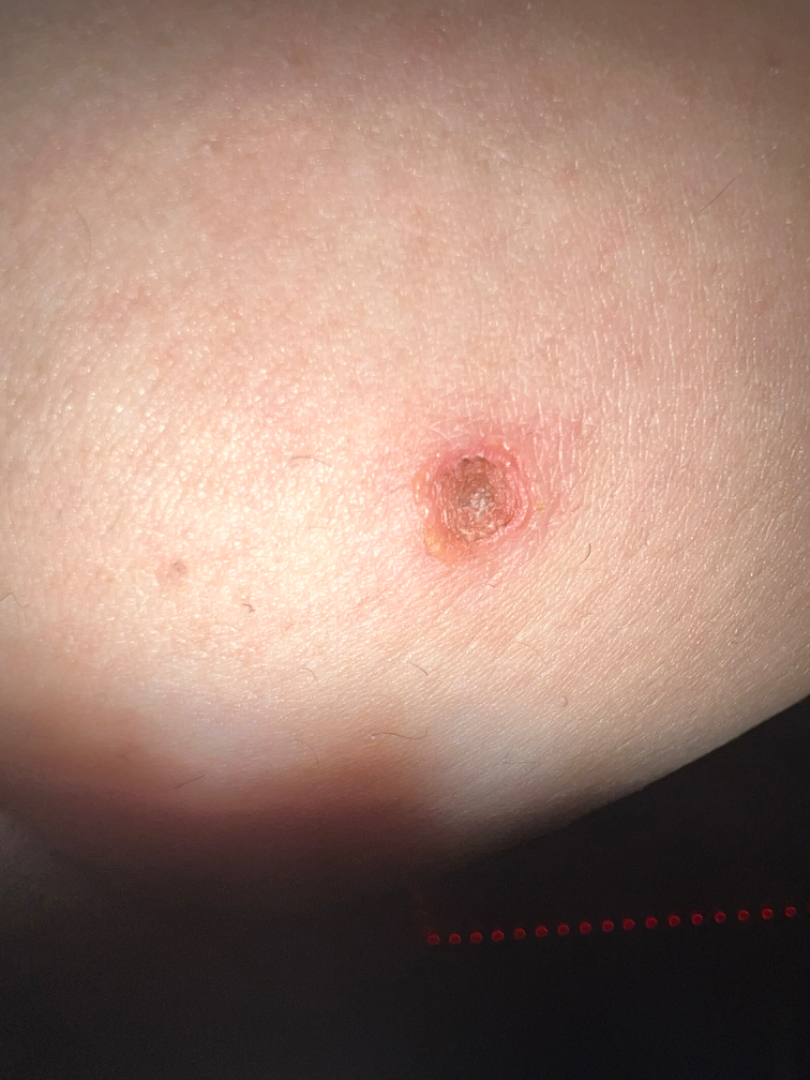On remote review of the image, Basal Cell Carcinoma (most likely); SCC/SCCIS (possible).